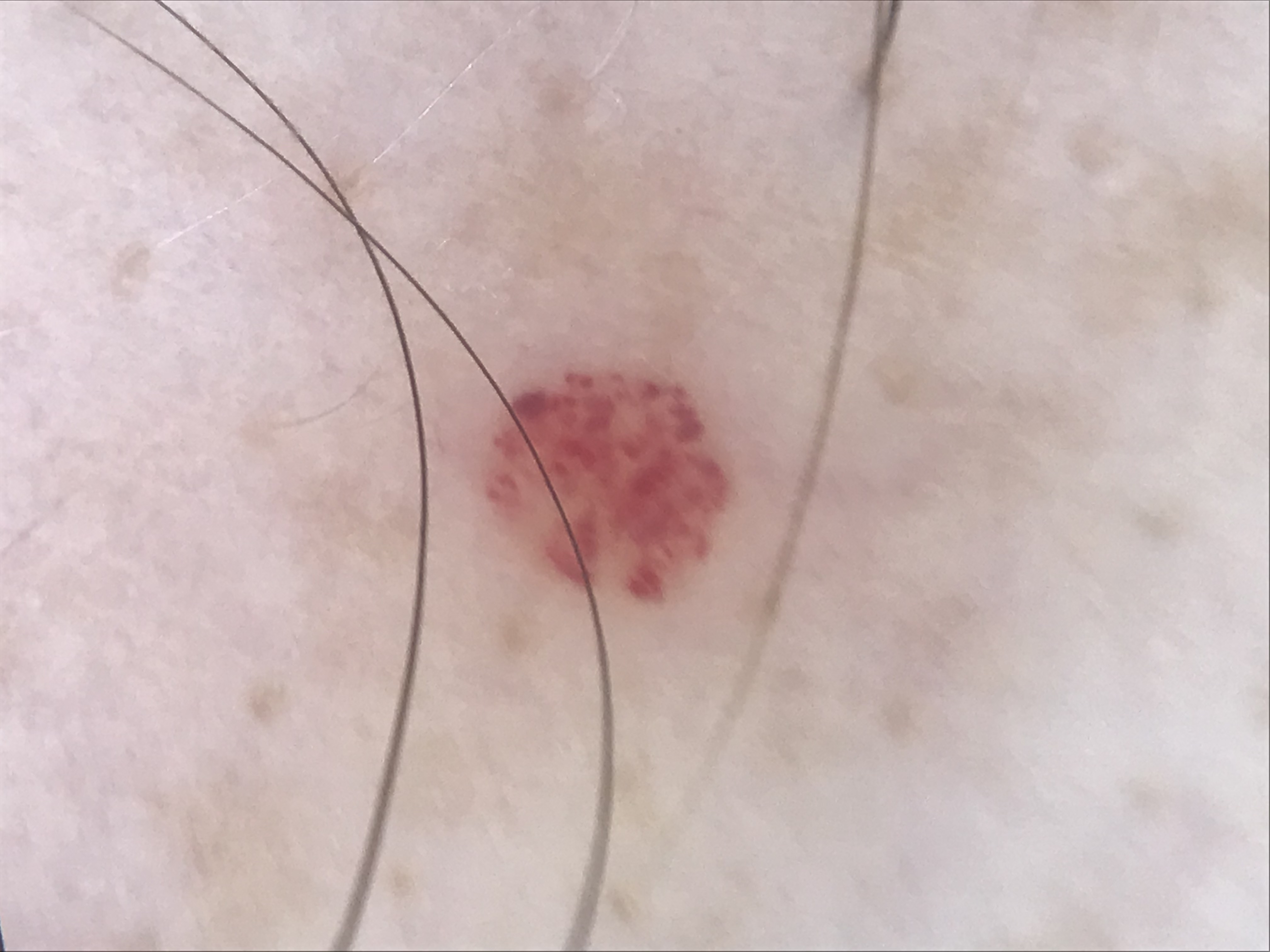| field | value |
|---|---|
| classification | vascular |
| assessment | hemangioma (expert consensus) |